Dermoscopy of a skin lesion.
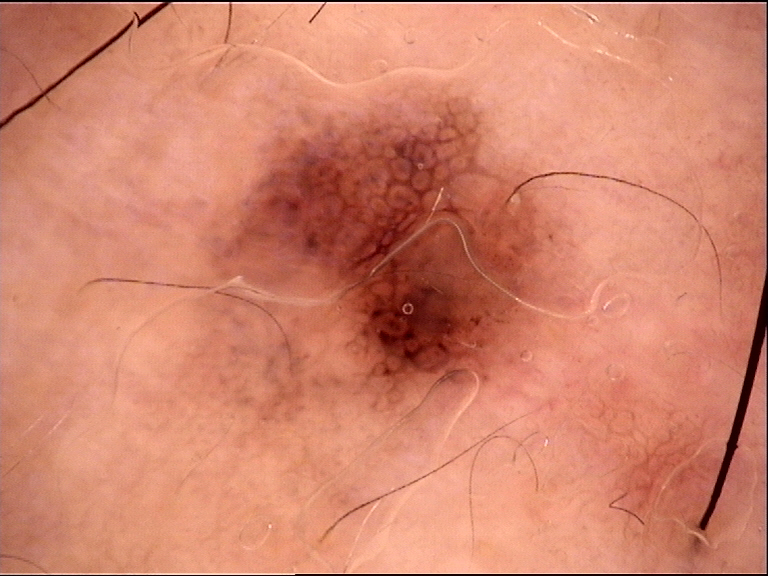Diagnosed as a dysplastic junctional nevus.